The contributor is a male aged 18–29; this is a close-up image; located on the head or neck.
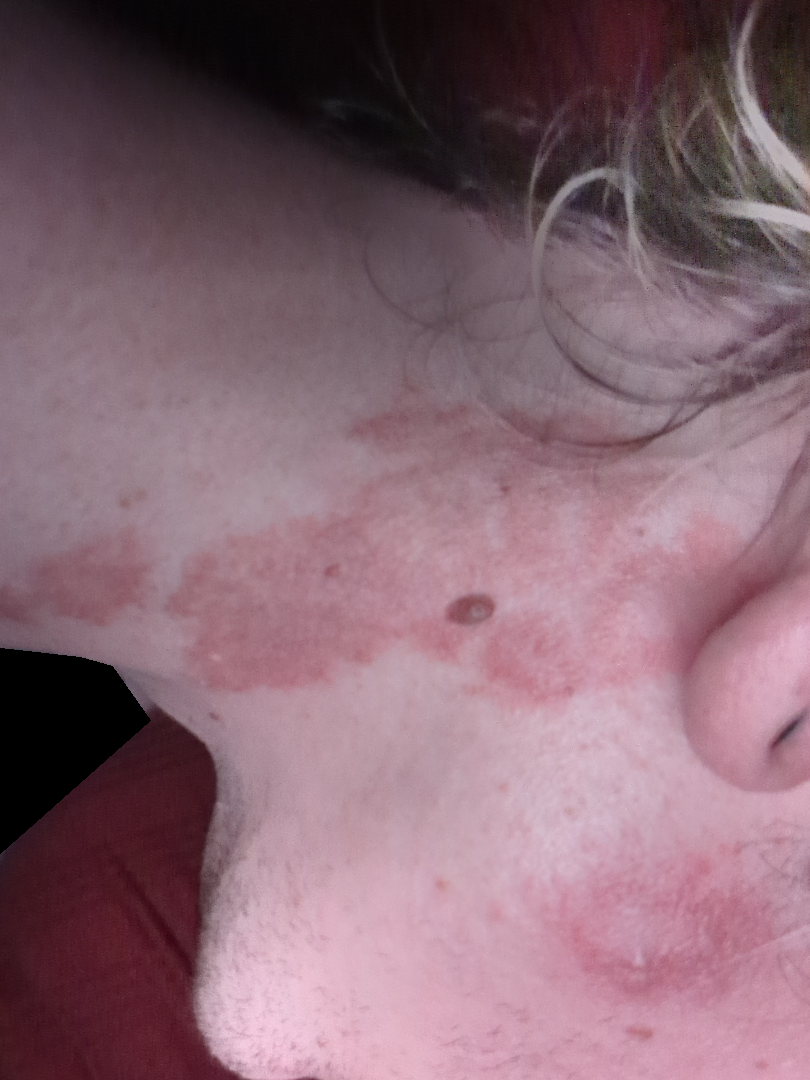Case summary:
– duration · since childhood
– skin tone · Fitzpatrick I
– patient's own categorization · a pigmentary problem
– associated systemic symptoms · none reported
– patient-reported symptoms · darkening
– diagnostic considerations · Tinea (considered); Allergic Contact Dermatitis (considered); Cutaneous lupus (considered)